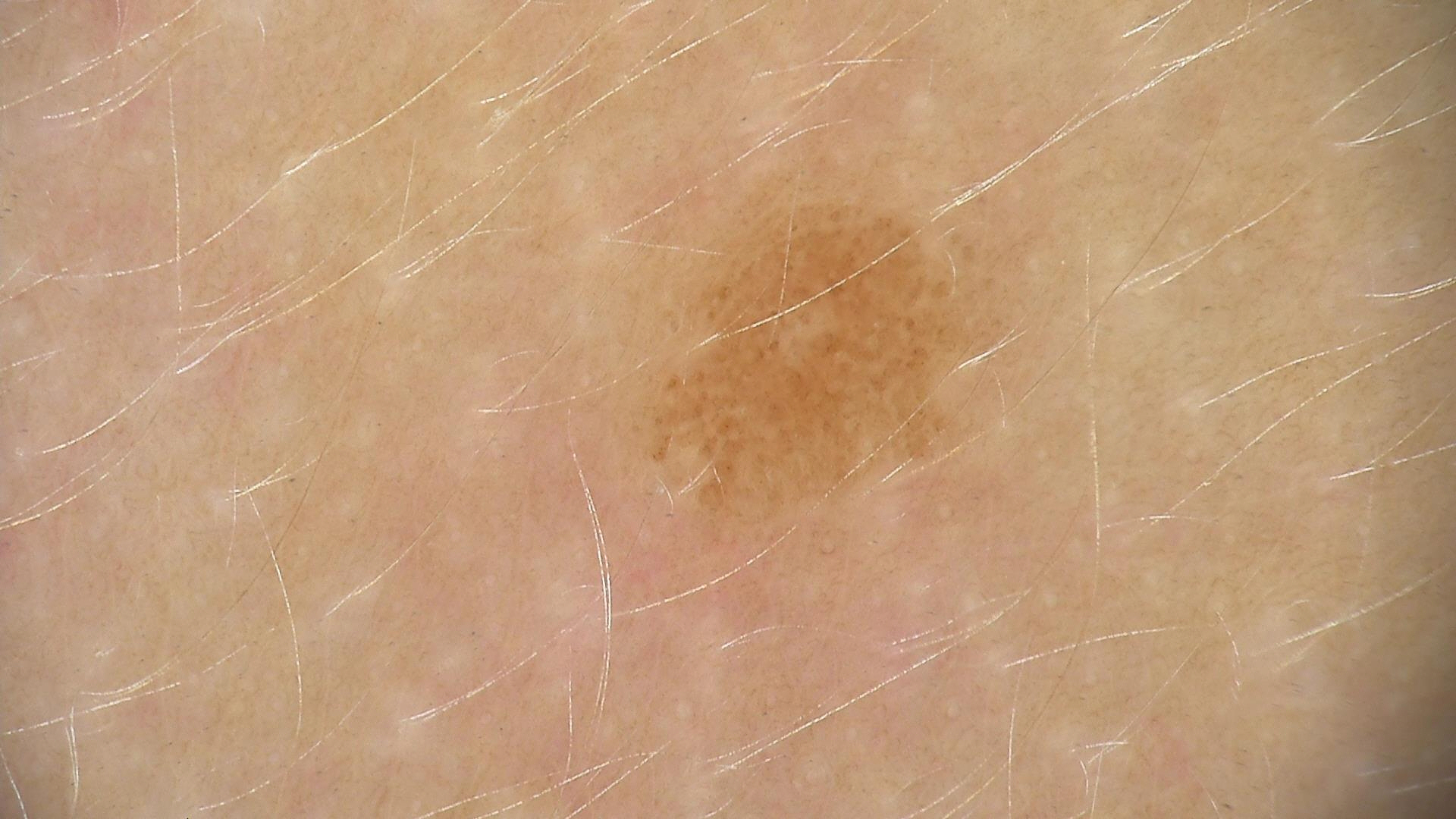Q: What is the diagnosis?
A: dysplastic junctional nevus (expert consensus)